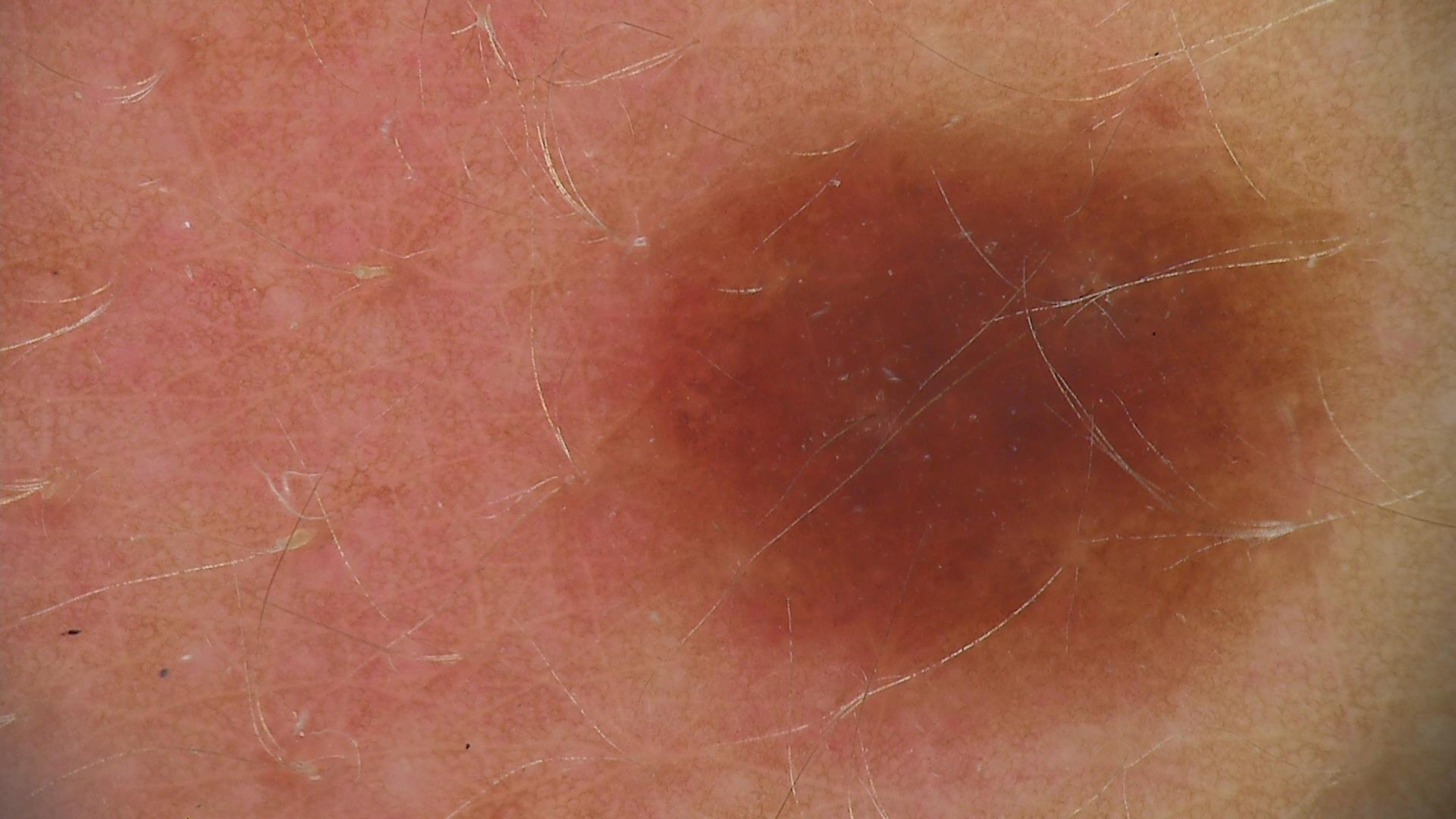Labeled as a benign lesion — a dysplastic junctional nevus.